A dermoscopy image of a single skin lesion.
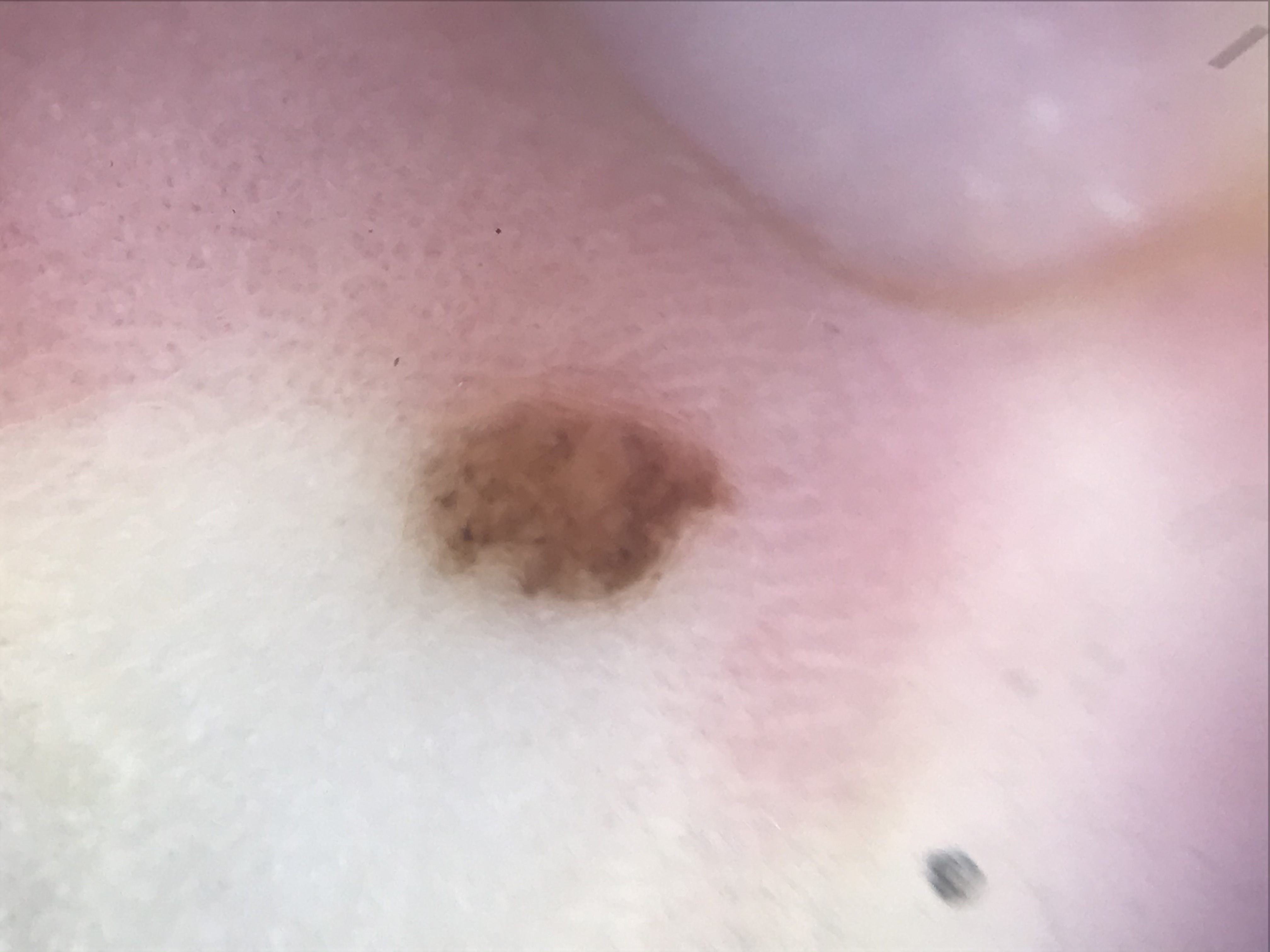Impression:
The diagnosis was a banal lesion — an acral compound nevus.